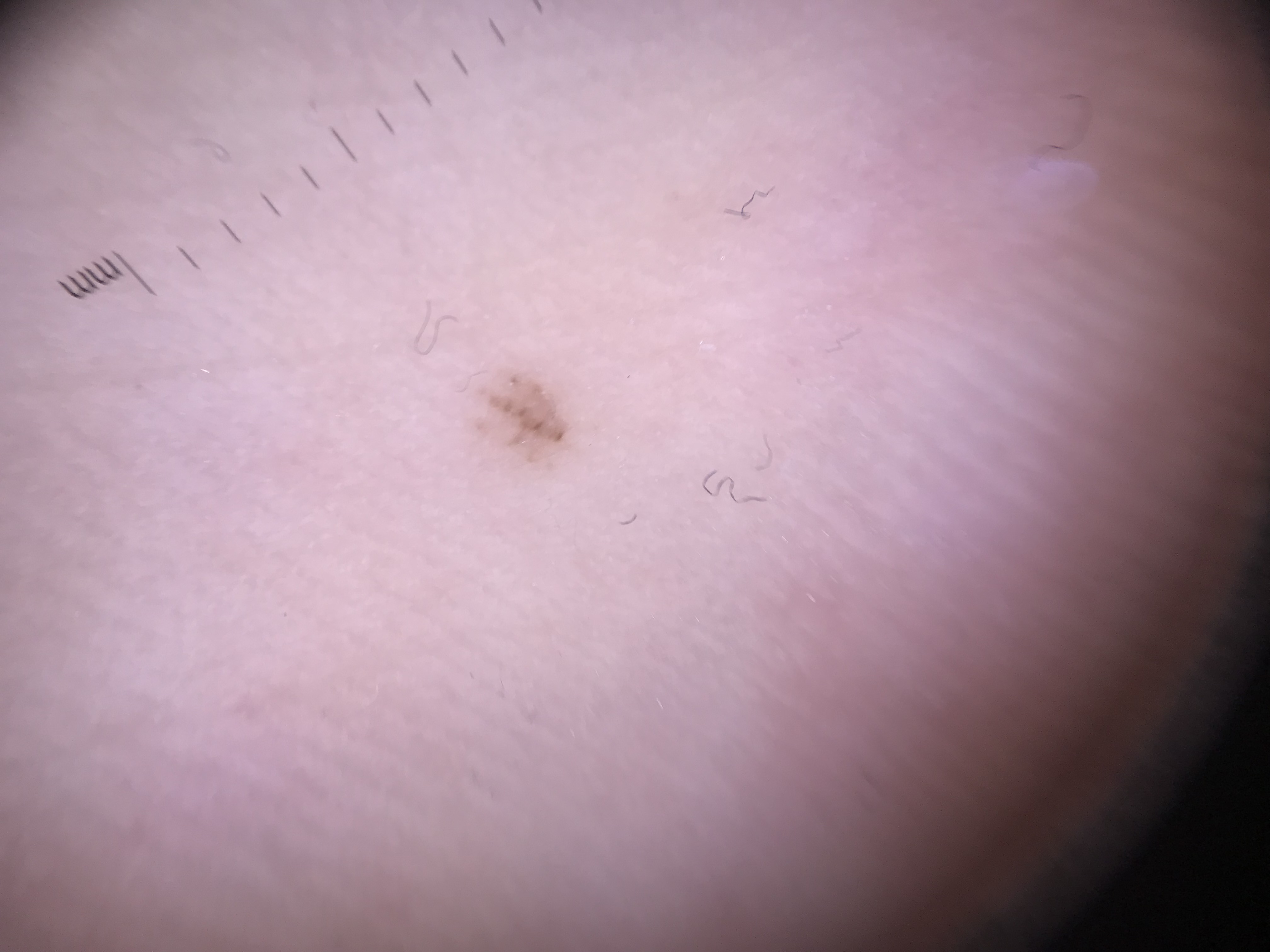{
  "diagnosis": {
    "name": "acral junctional nevus",
    "code": "ajb",
    "malignancy": "benign",
    "super_class": "melanocytic",
    "confirmation": "expert consensus"
  }
}